Symptoms reported: itching; the condition has been present for one to three months; located on the front of the torso; the patient reports the lesion is raised or bumpy; the contributor is 40–49, female; the photo was captured at an angle:
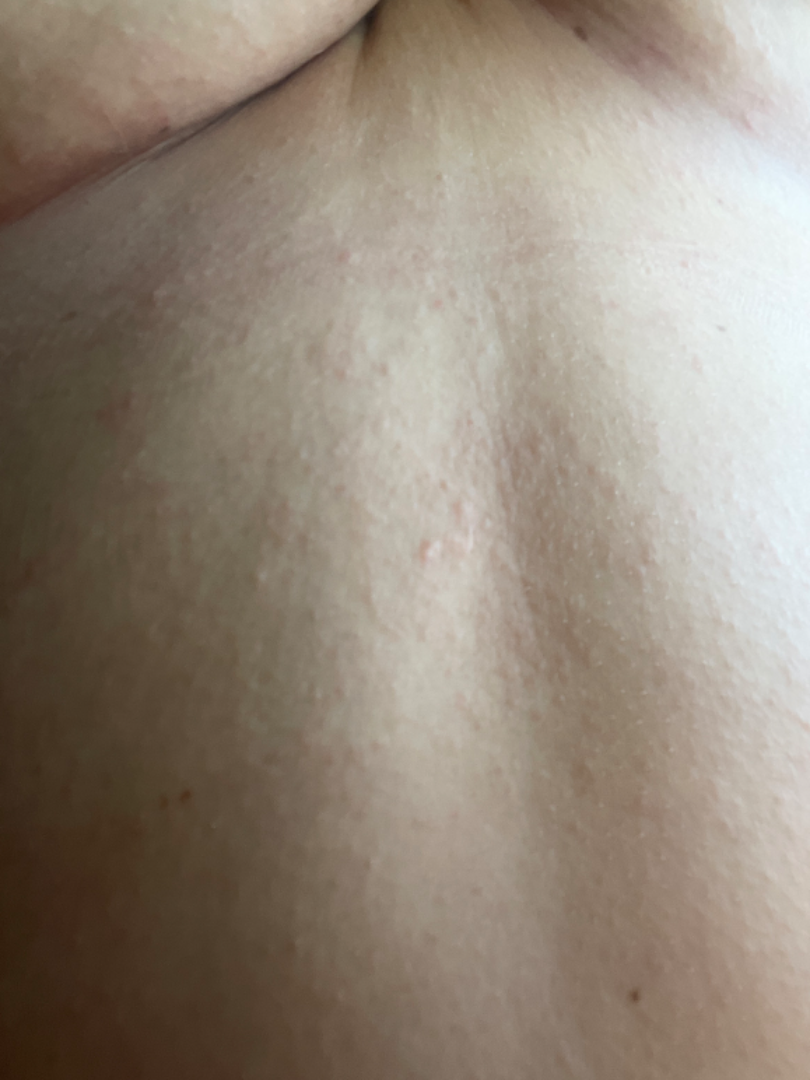On dermatologist assessment of the image: the differential includes Tinea Versicolor, Psoriasis and Eczema, with no clear leading consideration.